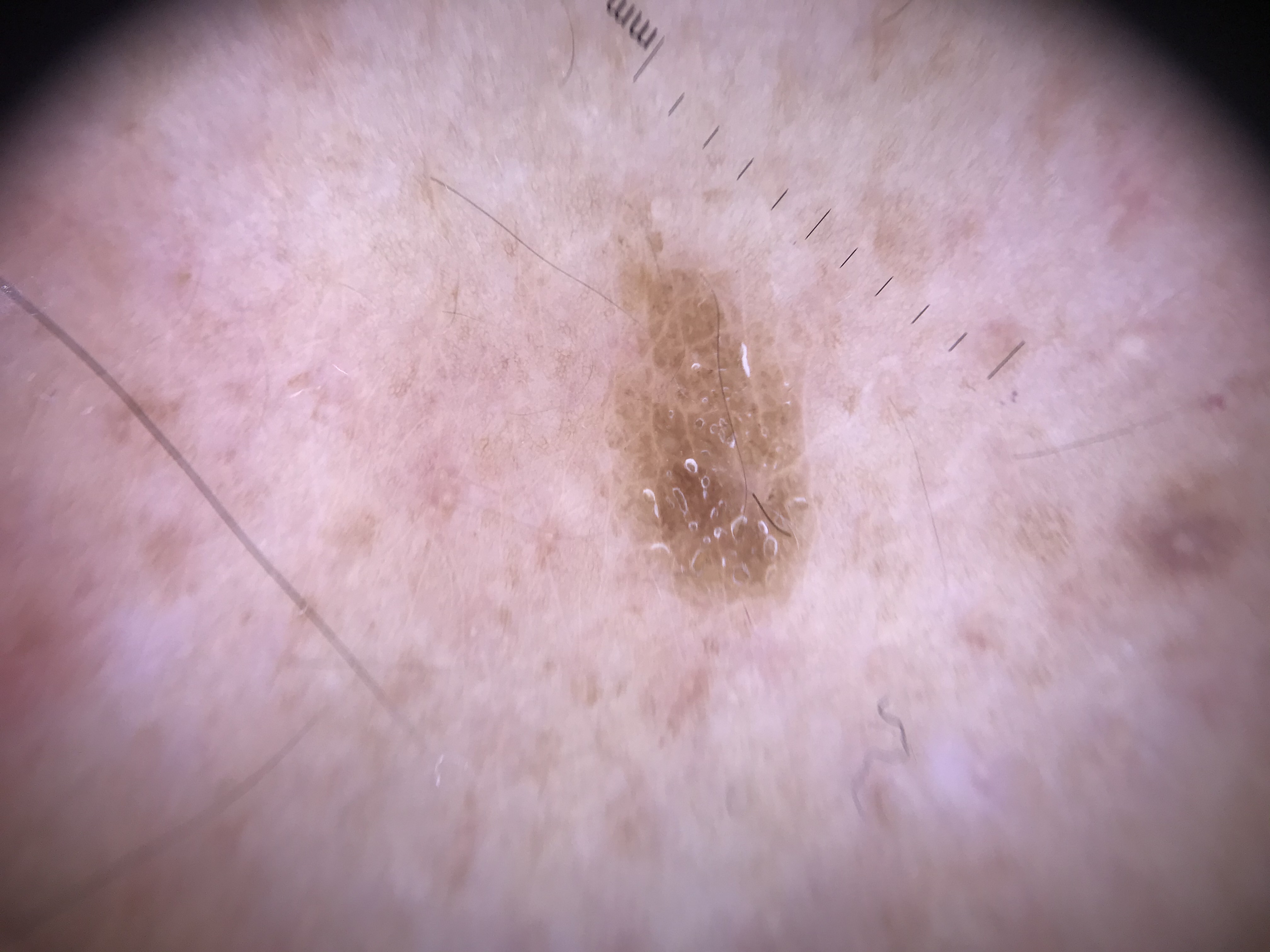Conclusion: The diagnostic label was a keratinocytic lesion — a seborrheic keratosis.